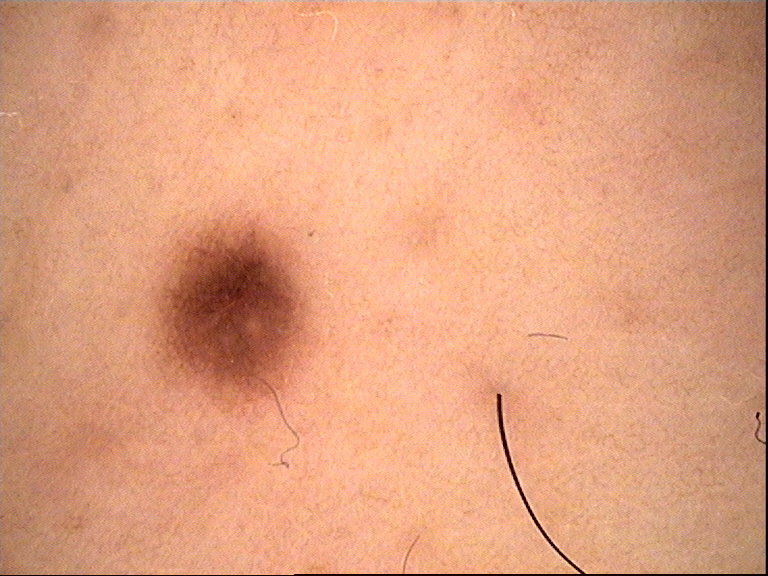assessment: dysplastic junctional nevus (expert consensus).